A skin lesion imaged with a dermatoscope: 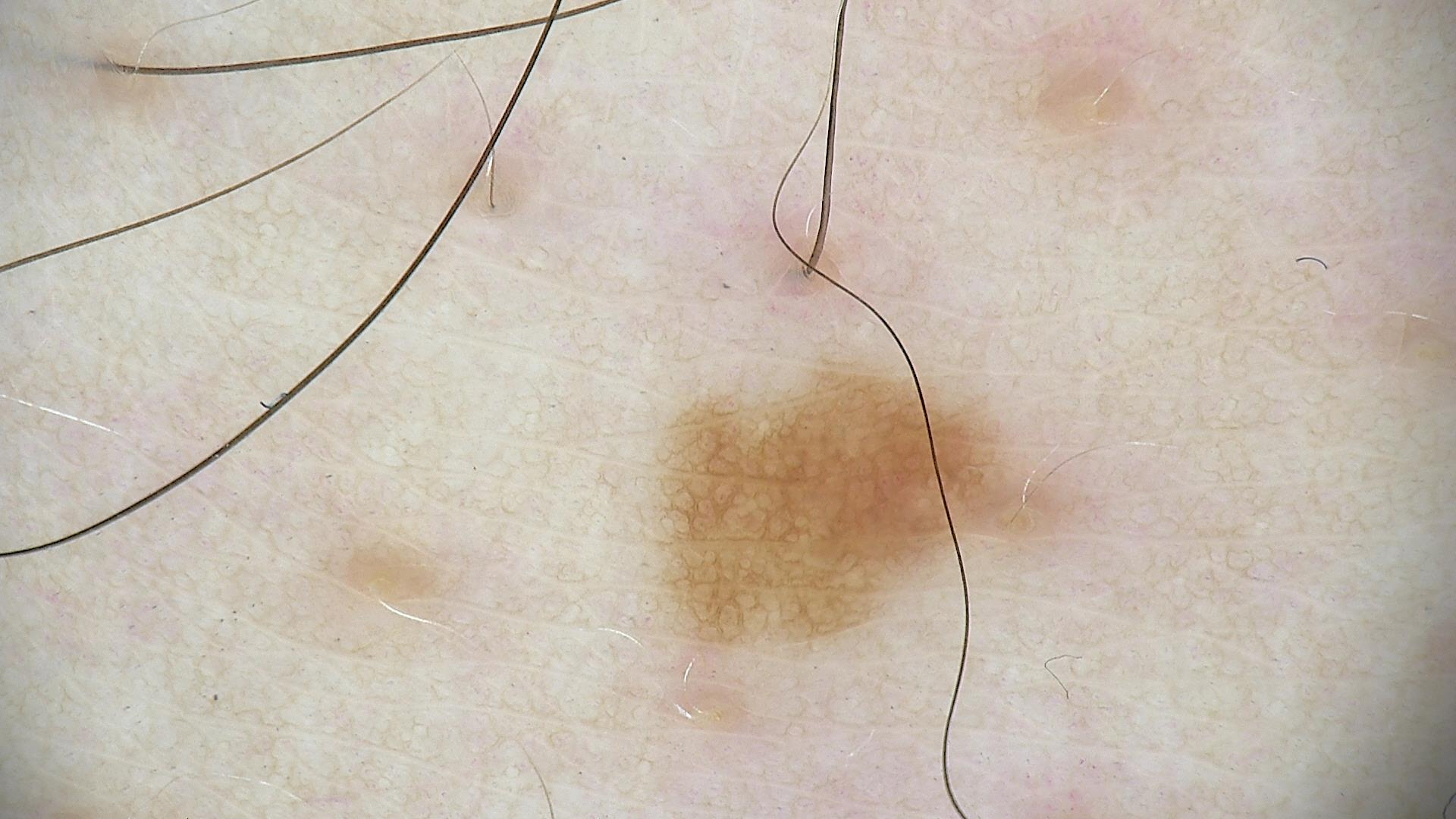Impression: The diagnostic label was a dysplastic junctional nevus.